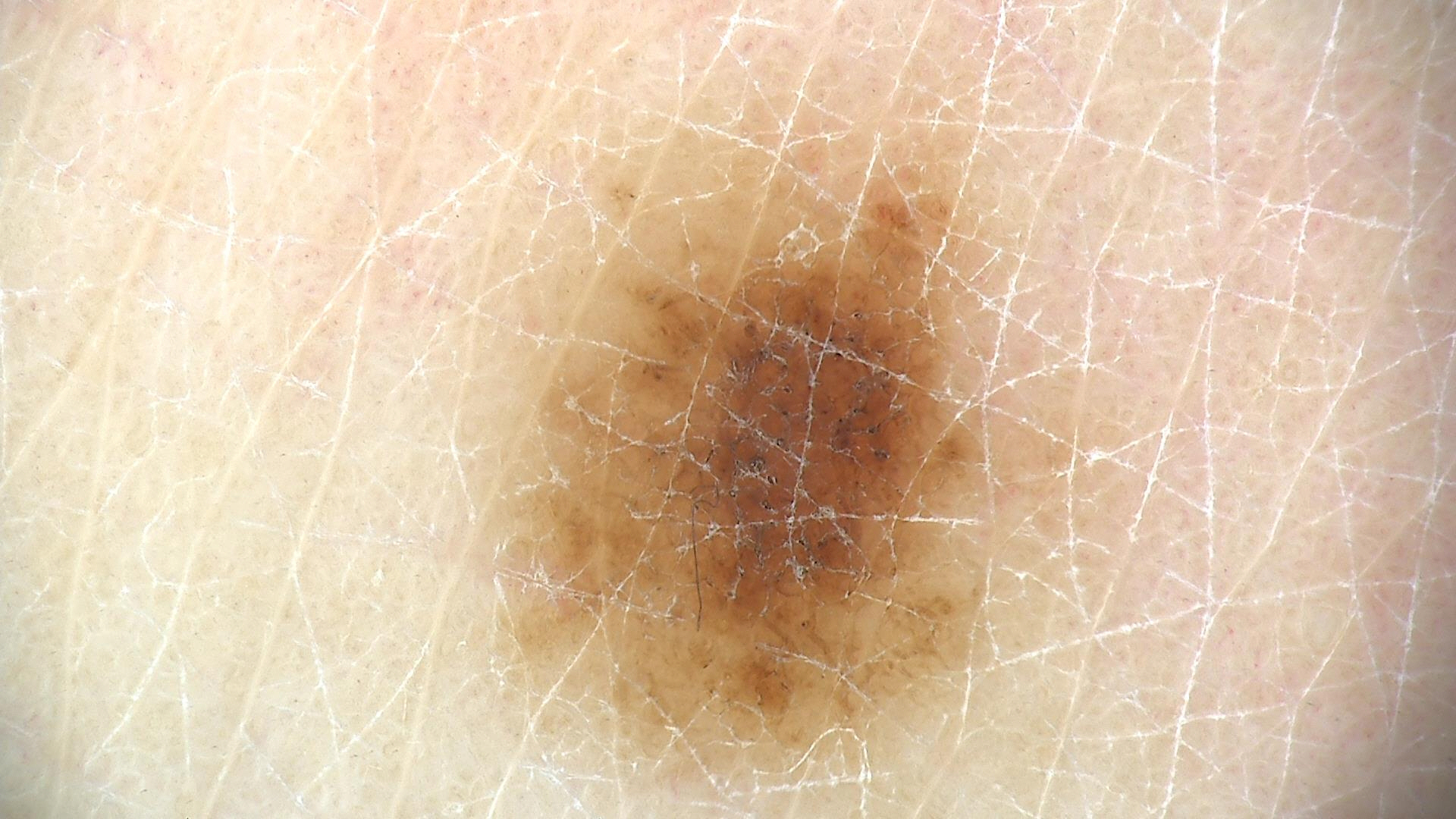image type=dermoscopy
diagnosis=dysplastic junctional nevus (expert consensus)